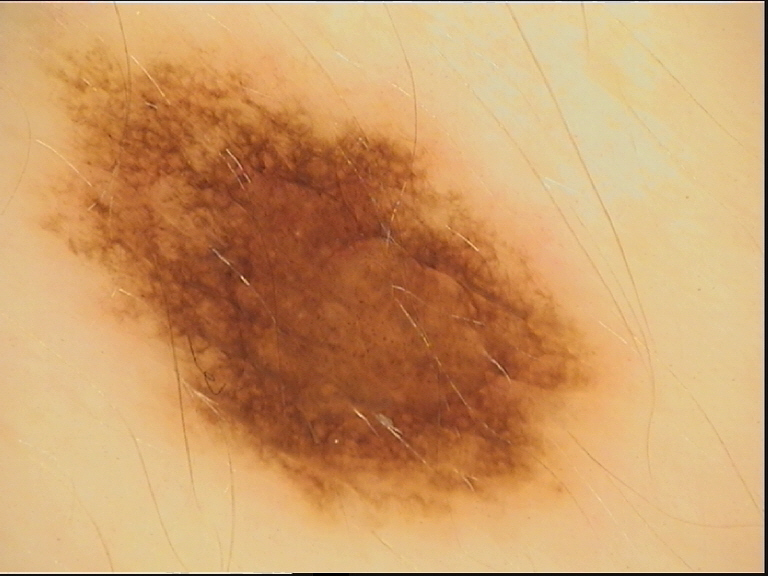Case:
• assessment: dysplastic junctional nevus (expert consensus)